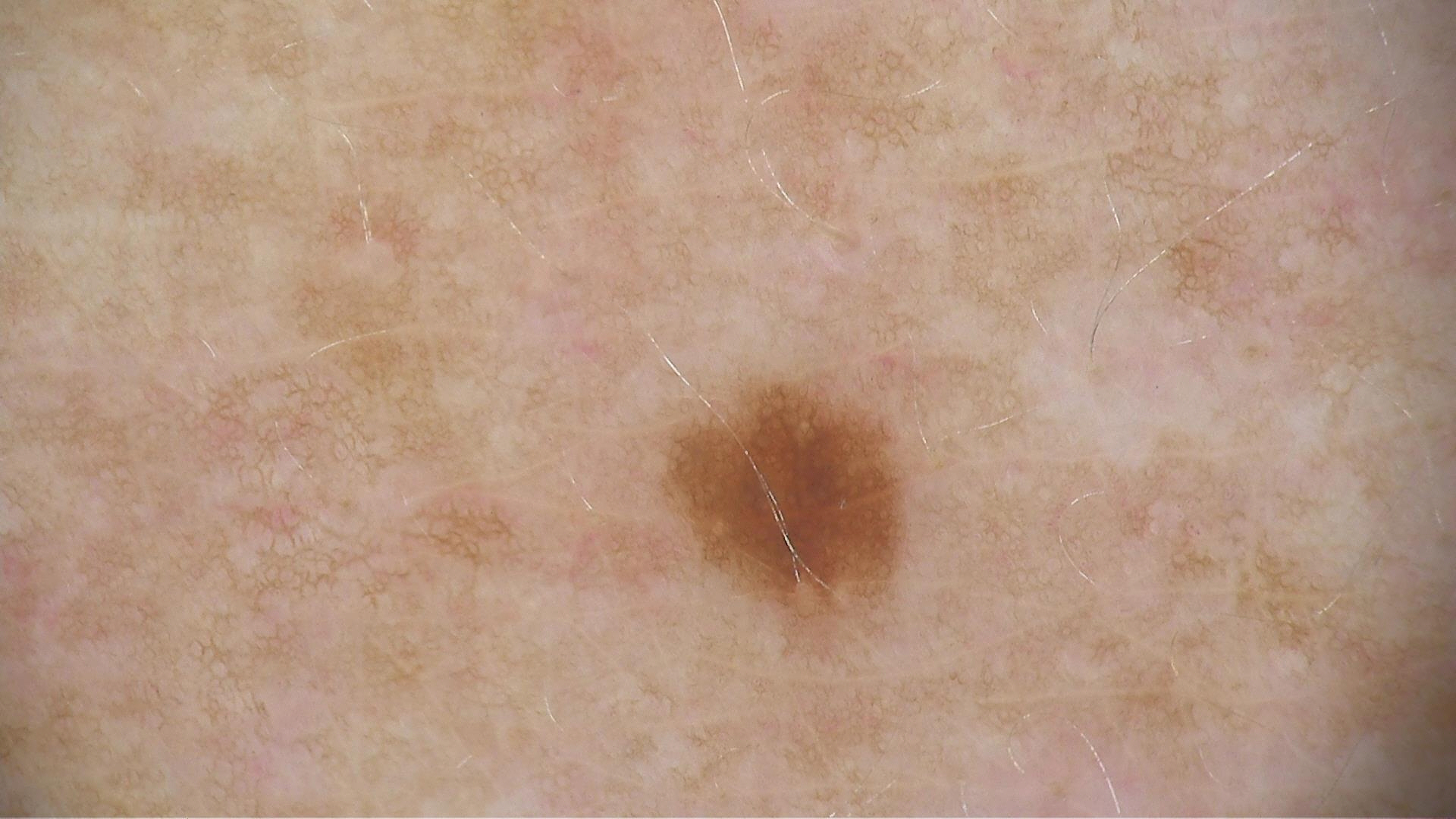Findings: A dermatoscopic image of a skin lesion. Conclusion: The diagnostic label was a dysplastic junctional nevus.